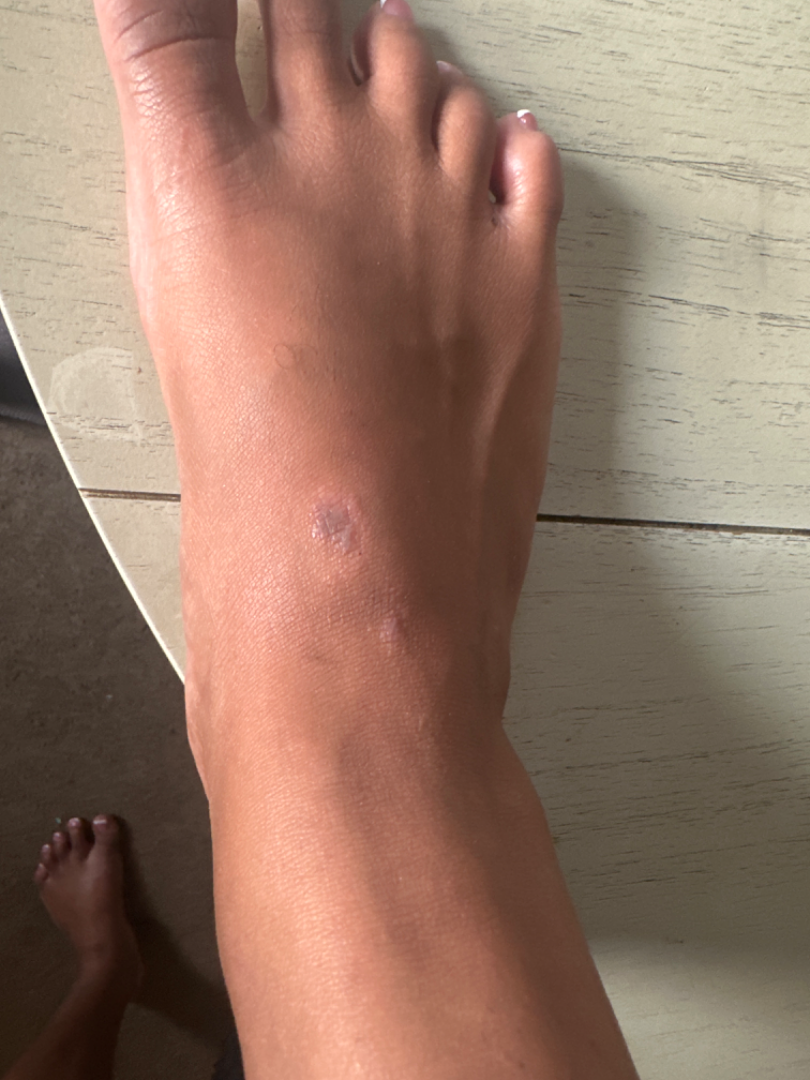Q: Patient's own categorization?
A: a rash
Q: When did this start?
A: three to twelve months
Q: Age and sex?
A: female, age 18–29
Q: What is the framing?
A: at a distance
Q: Where on the body?
A: leg and top or side of the foot
Q: What symptoms does the patient report?
A: enlargement, itching, bothersome appearance and darkening
Q: What is the differential diagnosis?
A: the differential is split between Lichen planus/lichenoid eruption, Lichen Simplex Chronicus and Insect Bite